A dermoscopic close-up of a skin lesion:
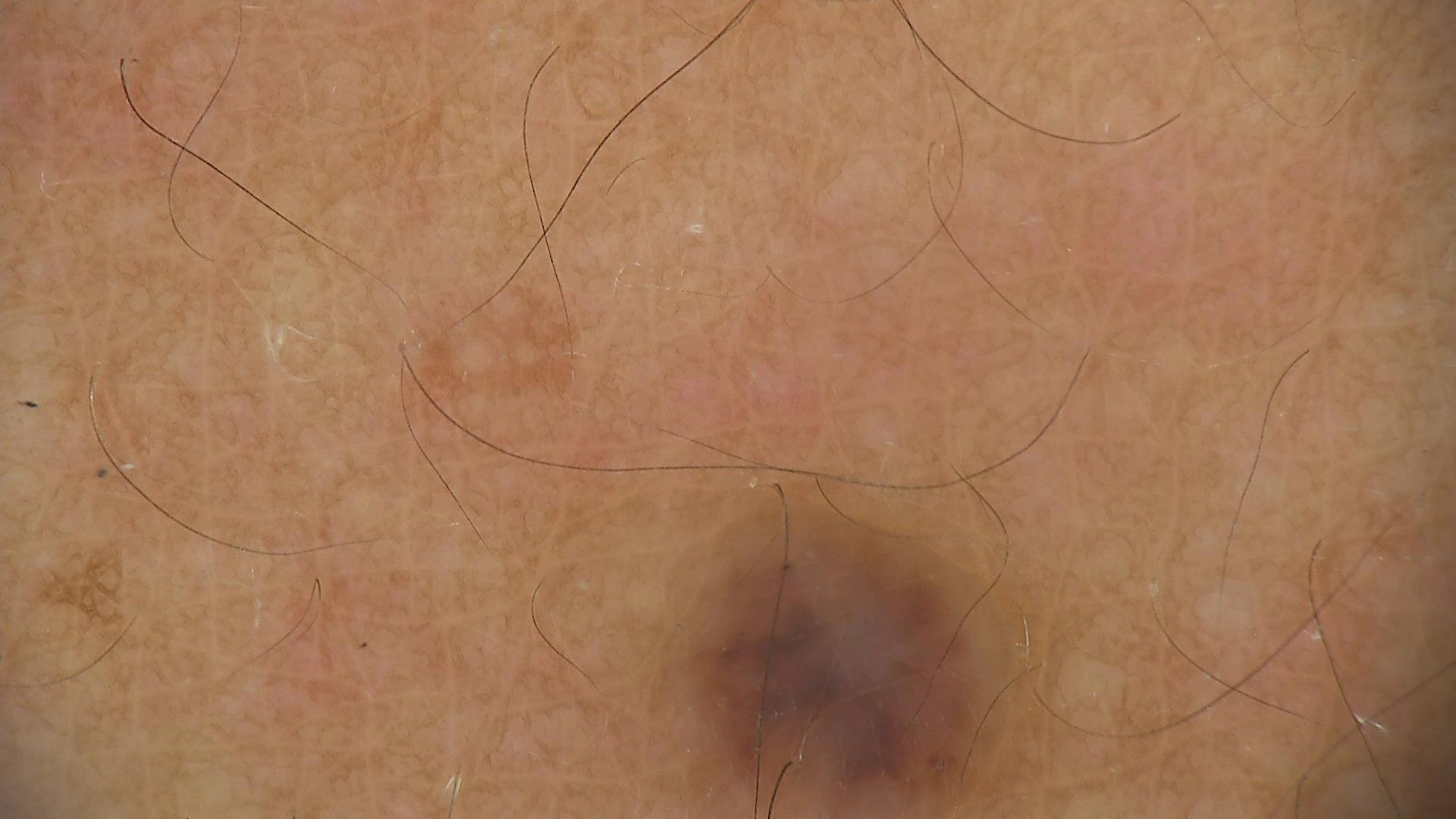Consistent with a banal lesion — a dermal nevus.